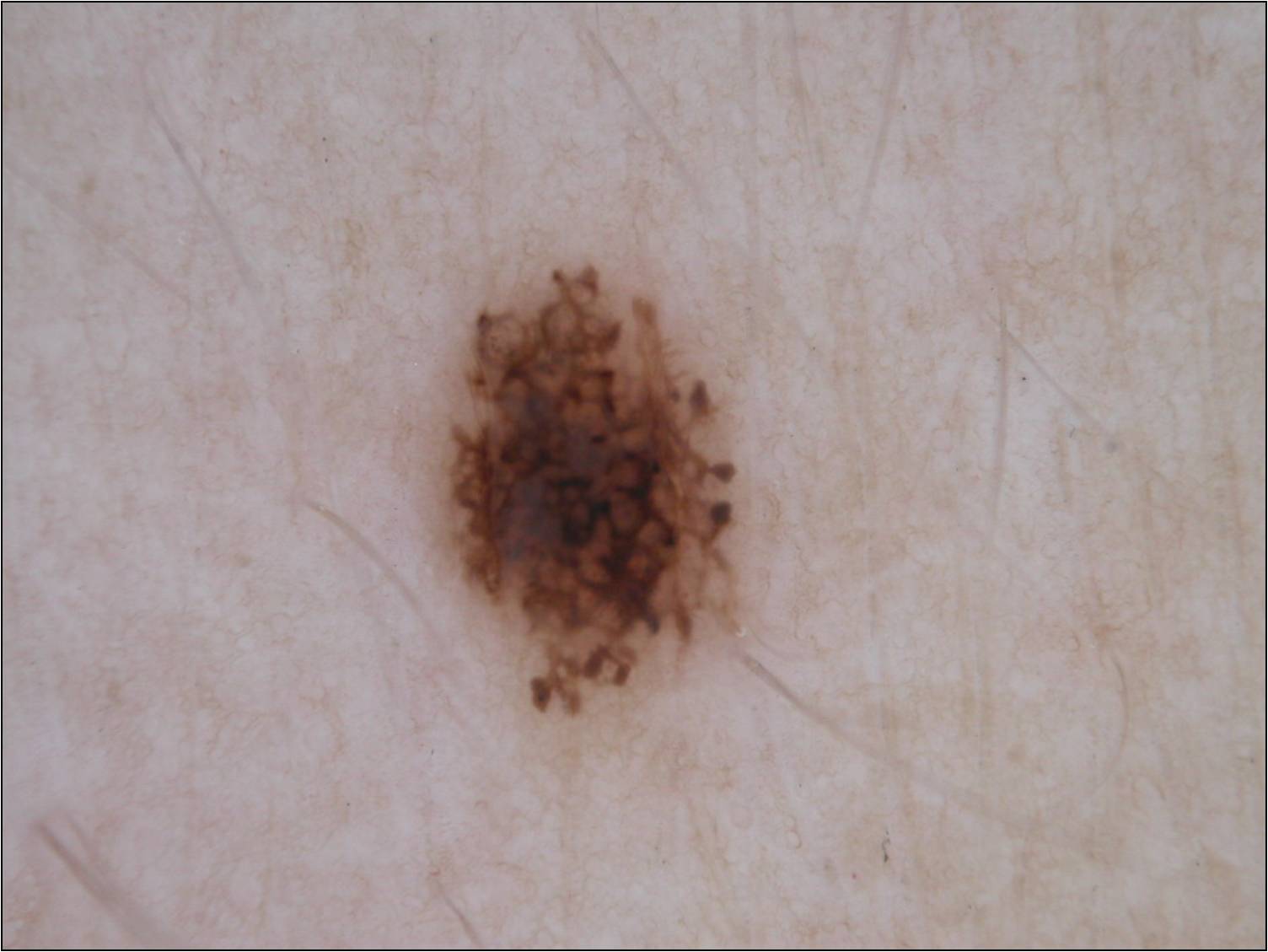A female subject roughly 40 years of age. A dermoscopic image of a skin lesion. A mid-sized lesion within the field. Dermoscopically, the lesion shows pigment network. With coordinates (x1, y1, x2, y2), the lesion is bounded by [428, 262, 735, 715]. Diagnosed as a melanocytic nevus, a benign lesion.